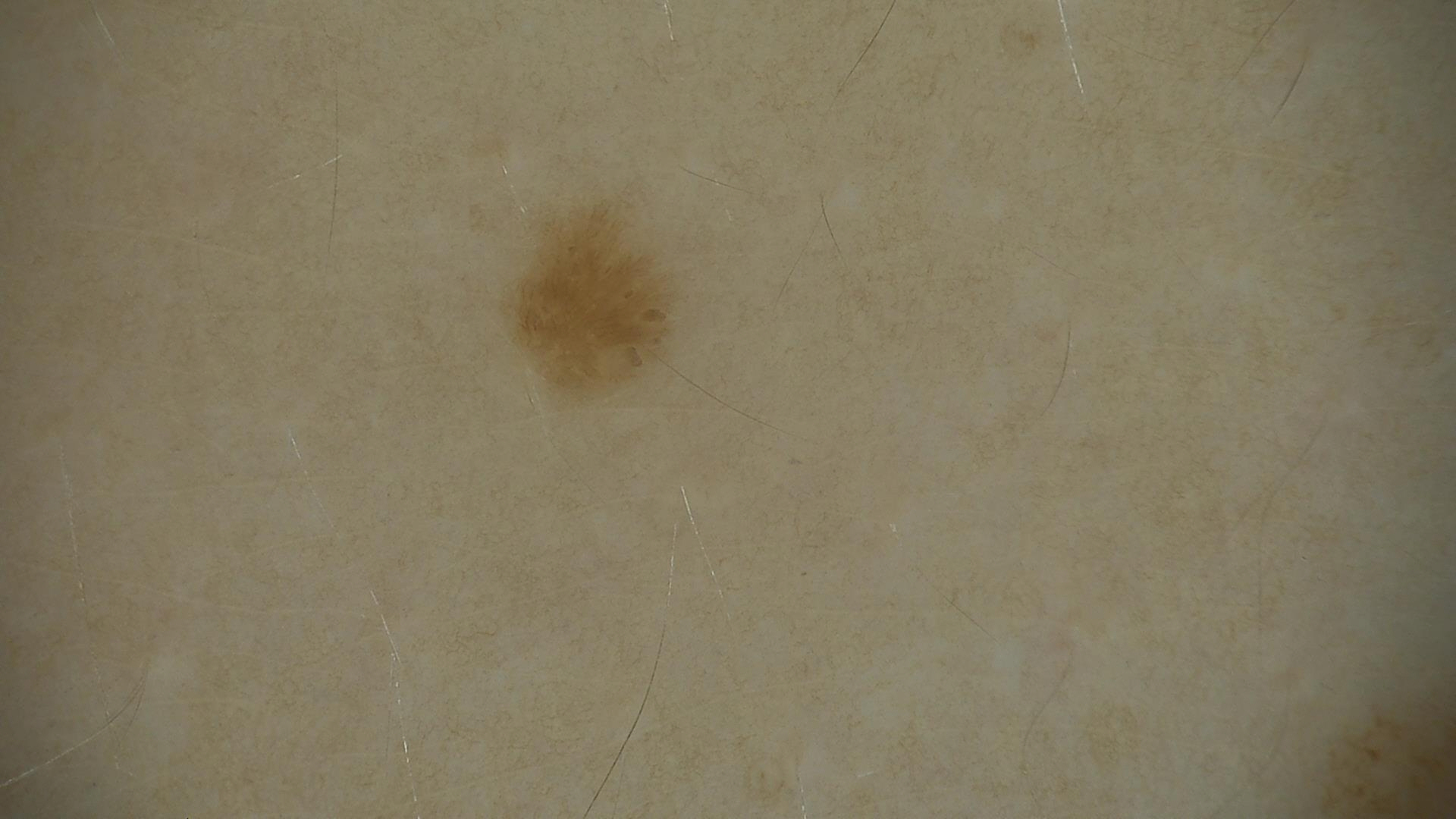Labeled as a benign lesion — a seborrheic keratosis.